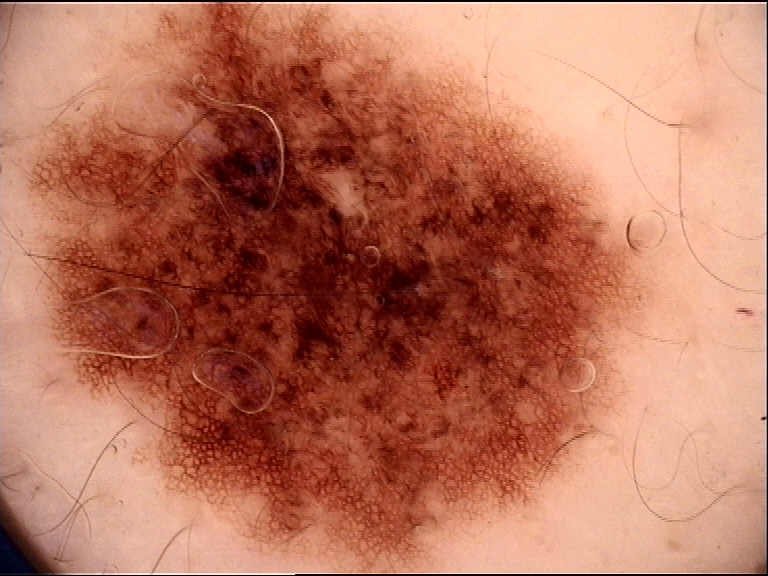modality — dermoscopy
diagnostic label — dysplastic junctional nevus (expert consensus)